A dermoscopy image of a single skin lesion:
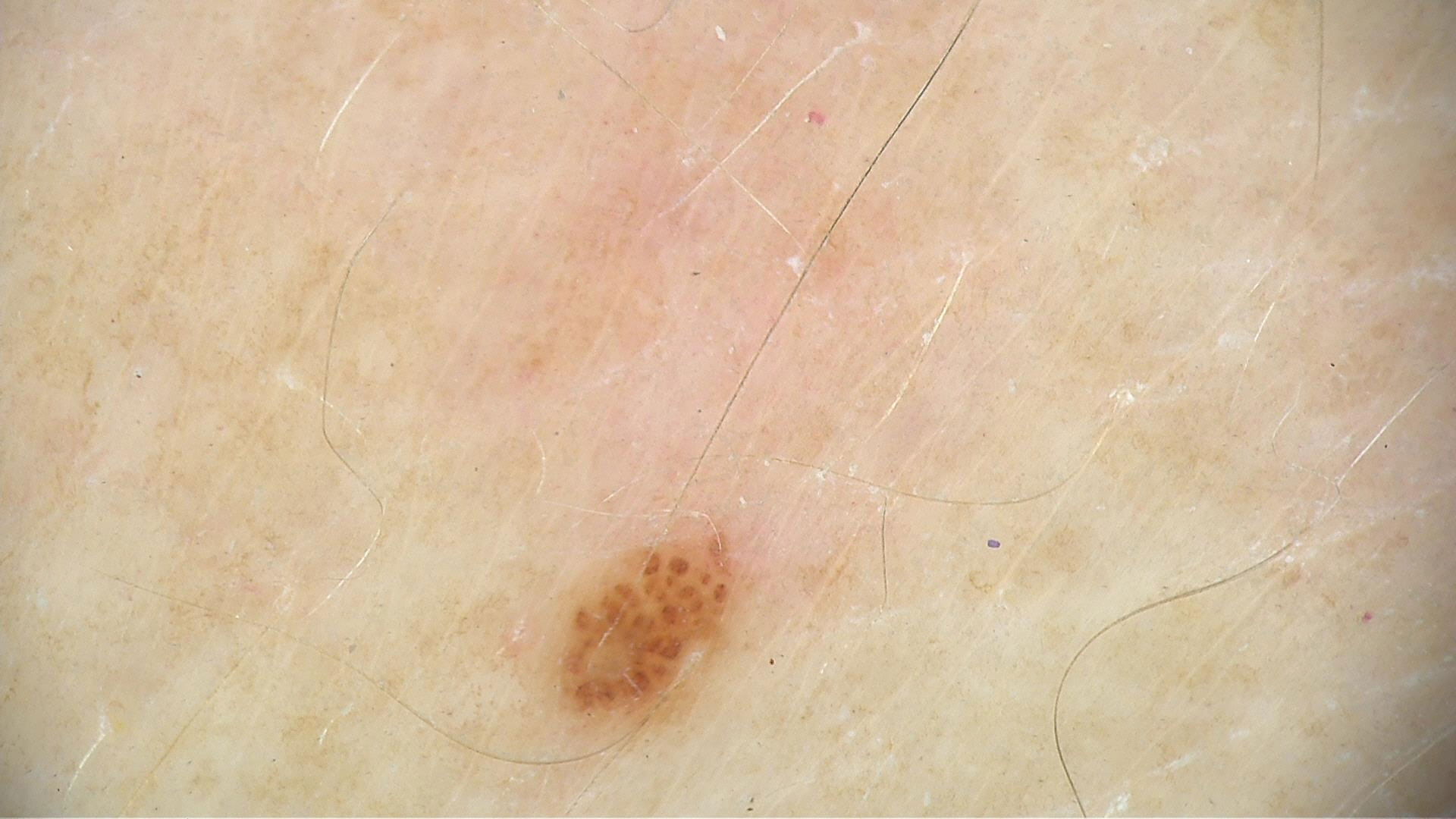Classified as a banal lesion — a junctional nevus.